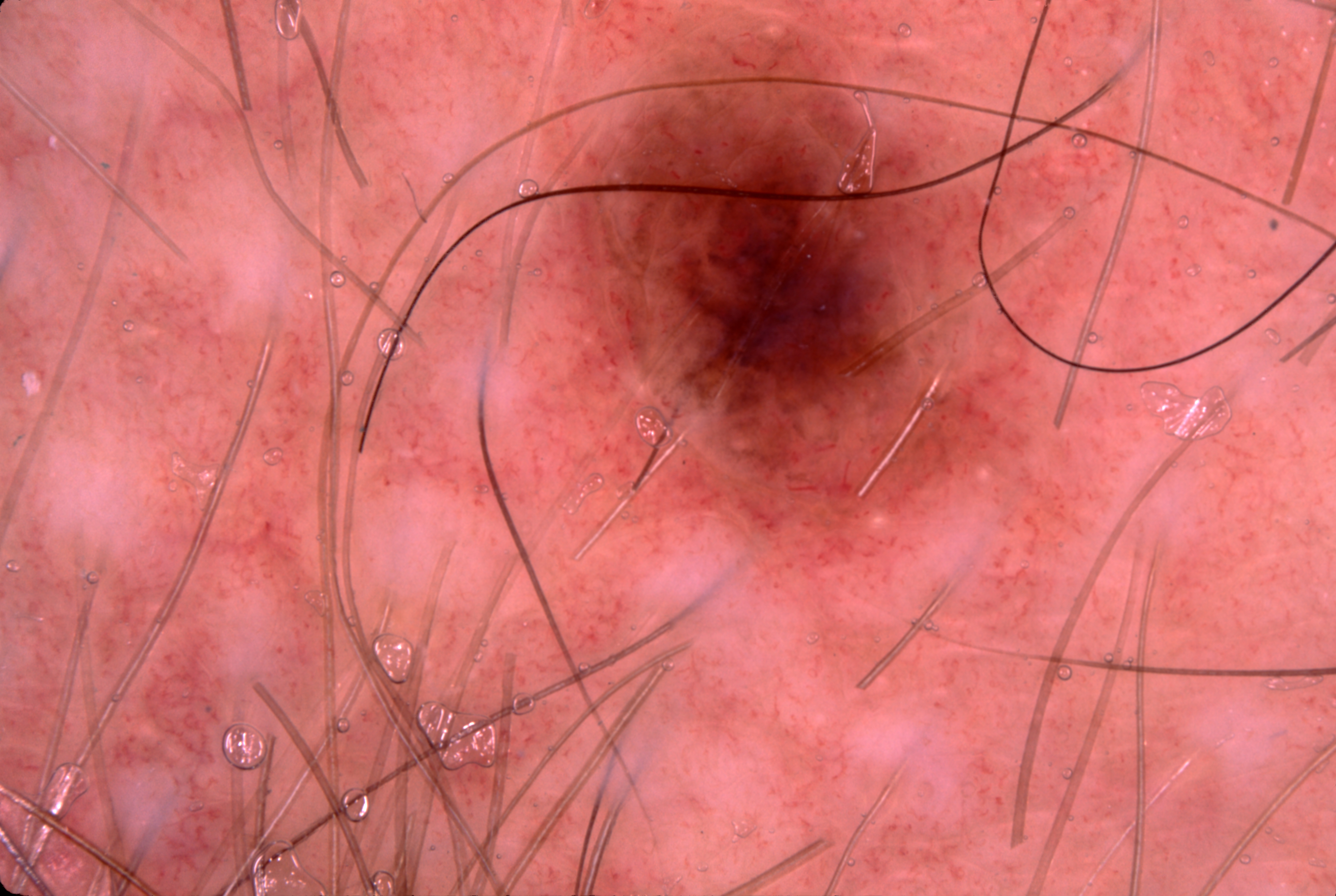Case summary:
Dermoscopy of a skin lesion. A male subject about 40 years old. The lesion occupies the region <box>563, 28, 1023, 560</box>. The lesion covers approximately 14% of the dermoscopic field. Dermoscopic examination shows milia-like cysts; no streaks, negative network, or pigment network.
Conclusion:
Diagnosed as a melanocytic nevus.